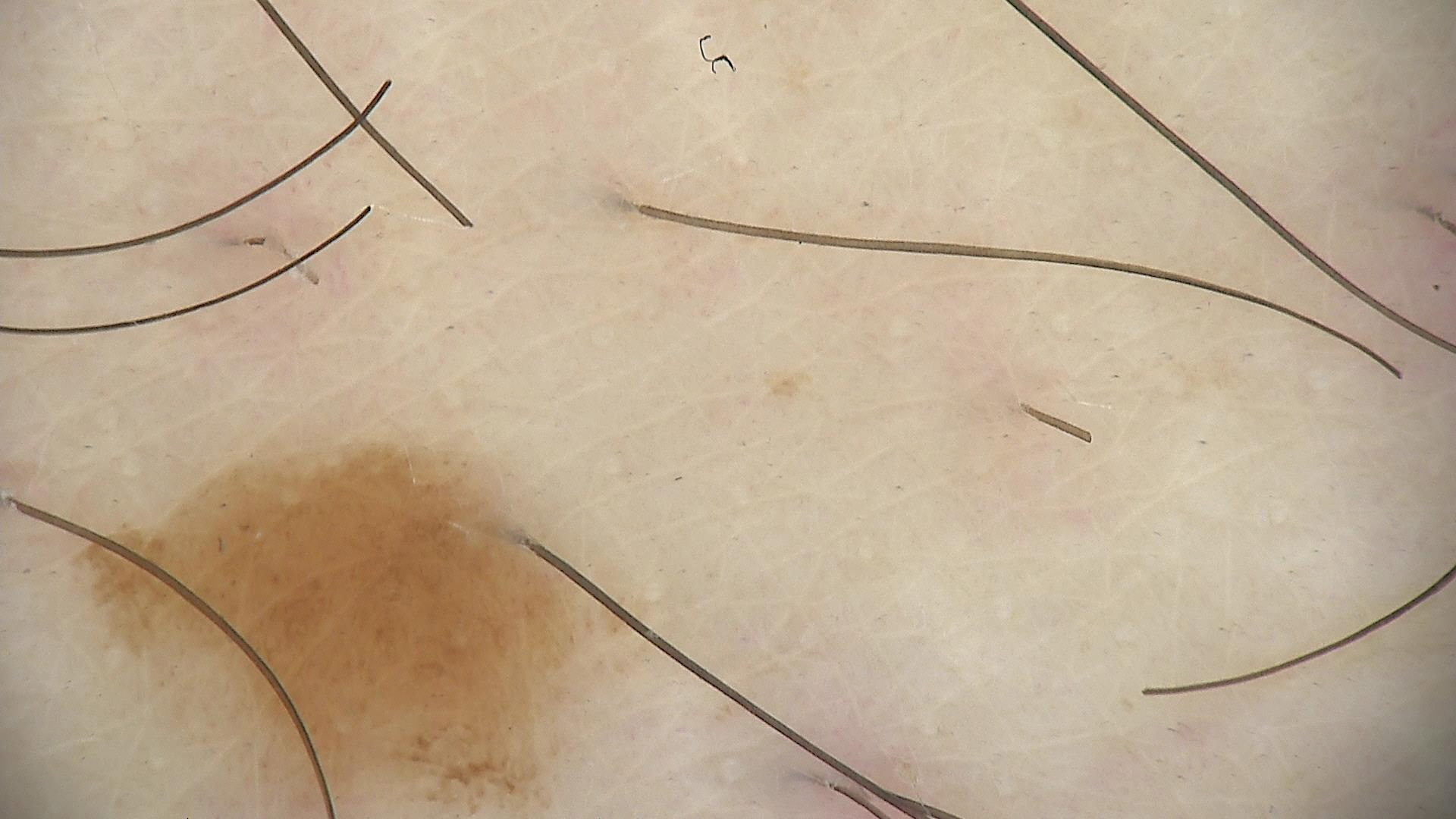lesion type: banal | label: junctional nevus (expert consensus).